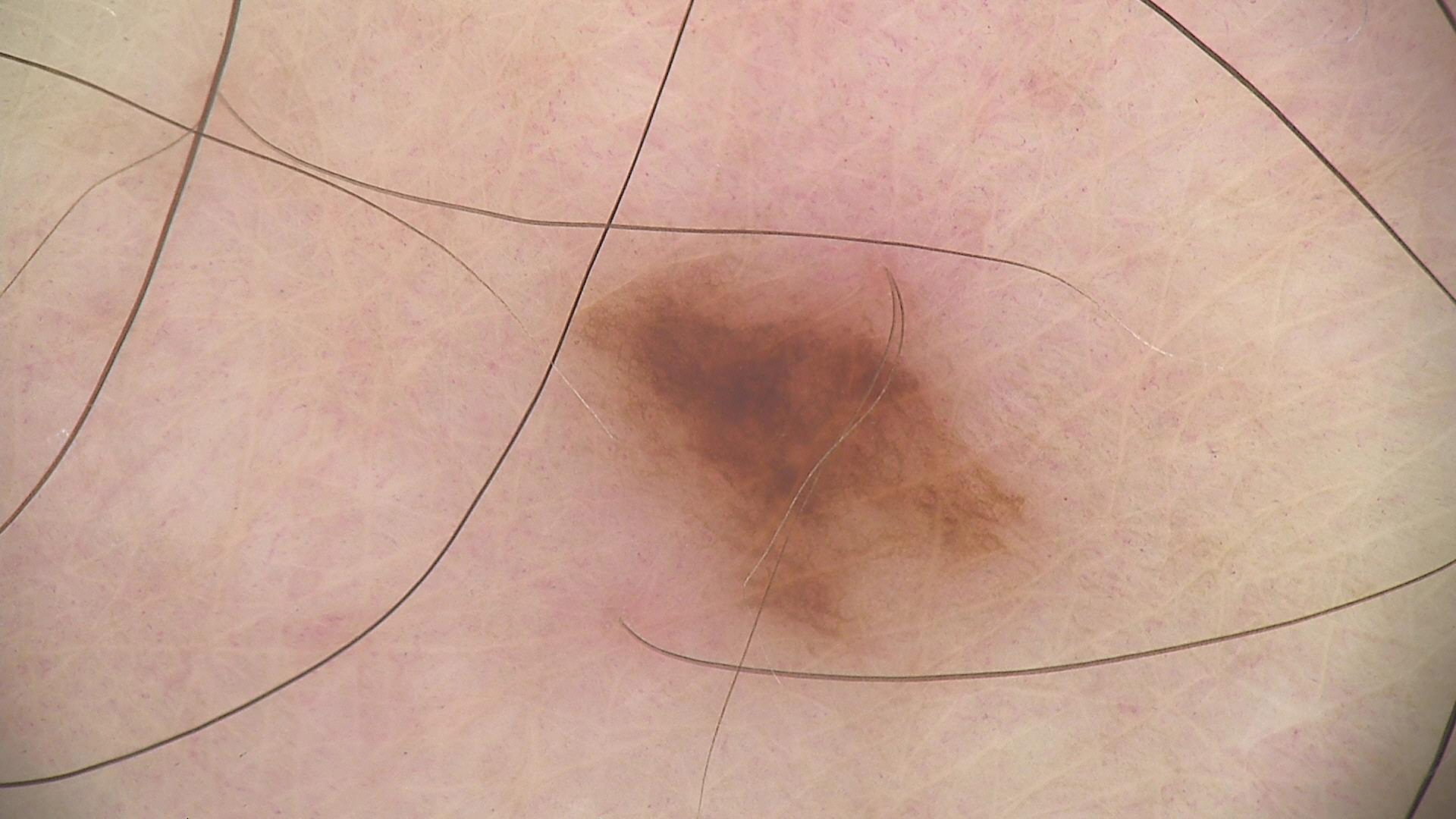| feature | finding |
|---|---|
| label | dysplastic junctional nevus (expert consensus) |